A dermatoscopic image of a skin lesion.
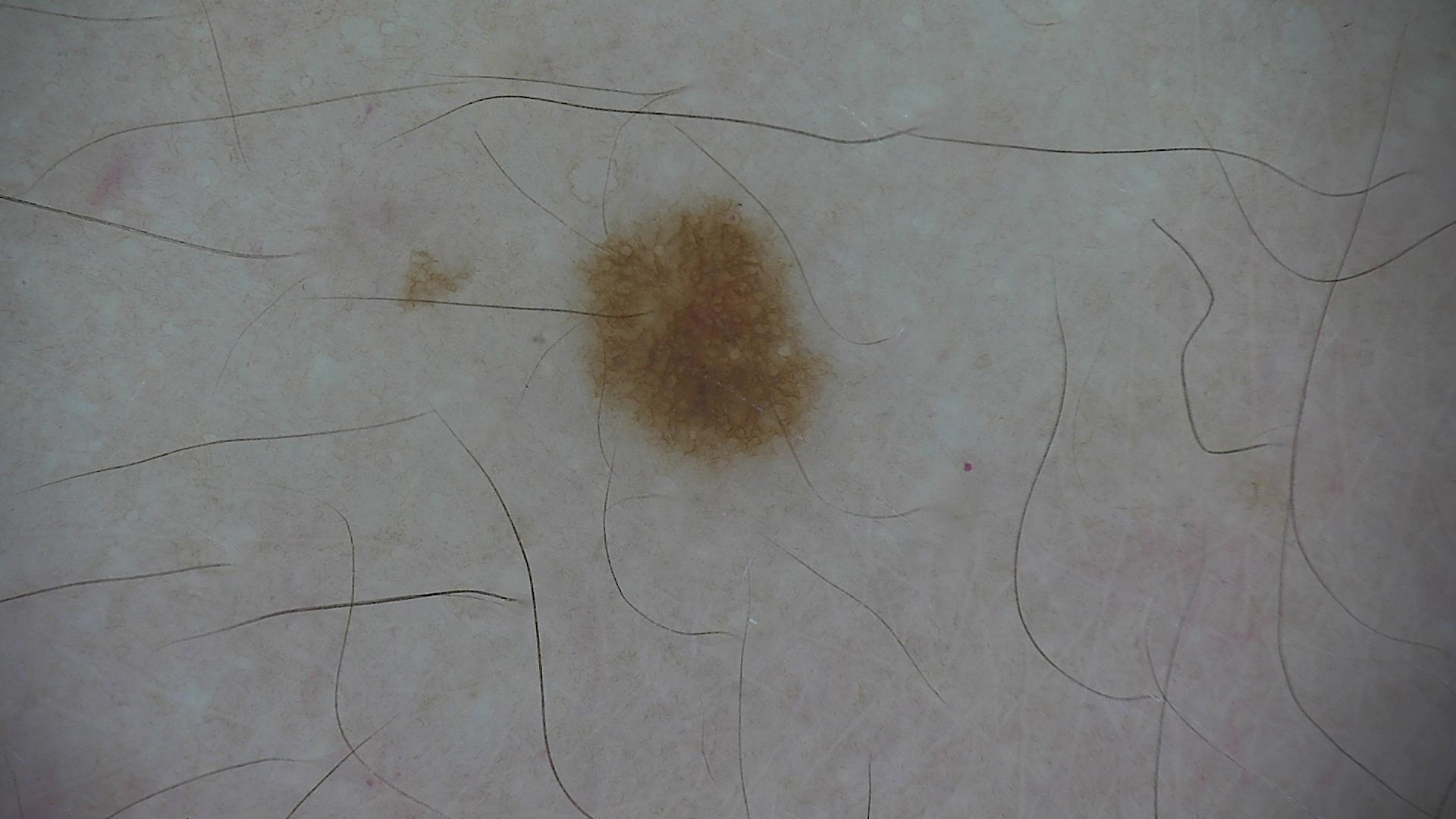Classified as a banal lesion — a junctional nevus.